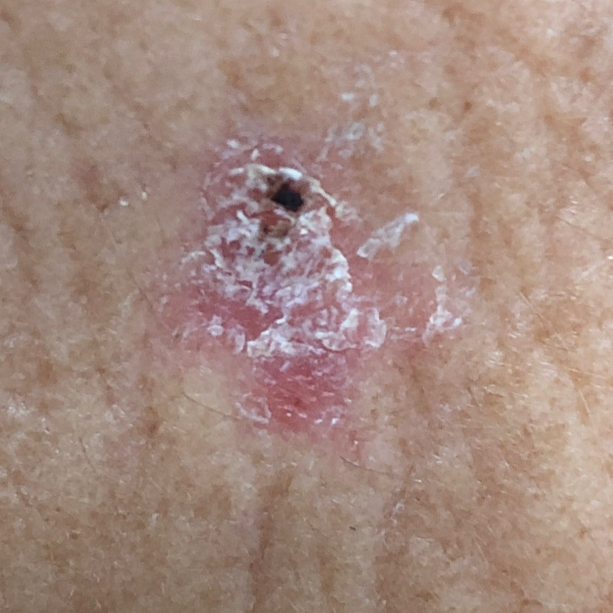Findings: A smartphone photograph of a skin lesion. The lesion is located on the face. The patient reports that the lesion itches. Conclusion: Consistent with a premalignant lesion — an actinic keratosis.